Reported duration is less than one week, the arm is involved, the patient is a male aged 18–29, the patient considered this a rash, texture is reported as raised or bumpy, skin tone: Fitzpatrick III; lay graders estimated 3 on the Monk skin tone scale, this image was taken at an angle, the patient indicates itching — 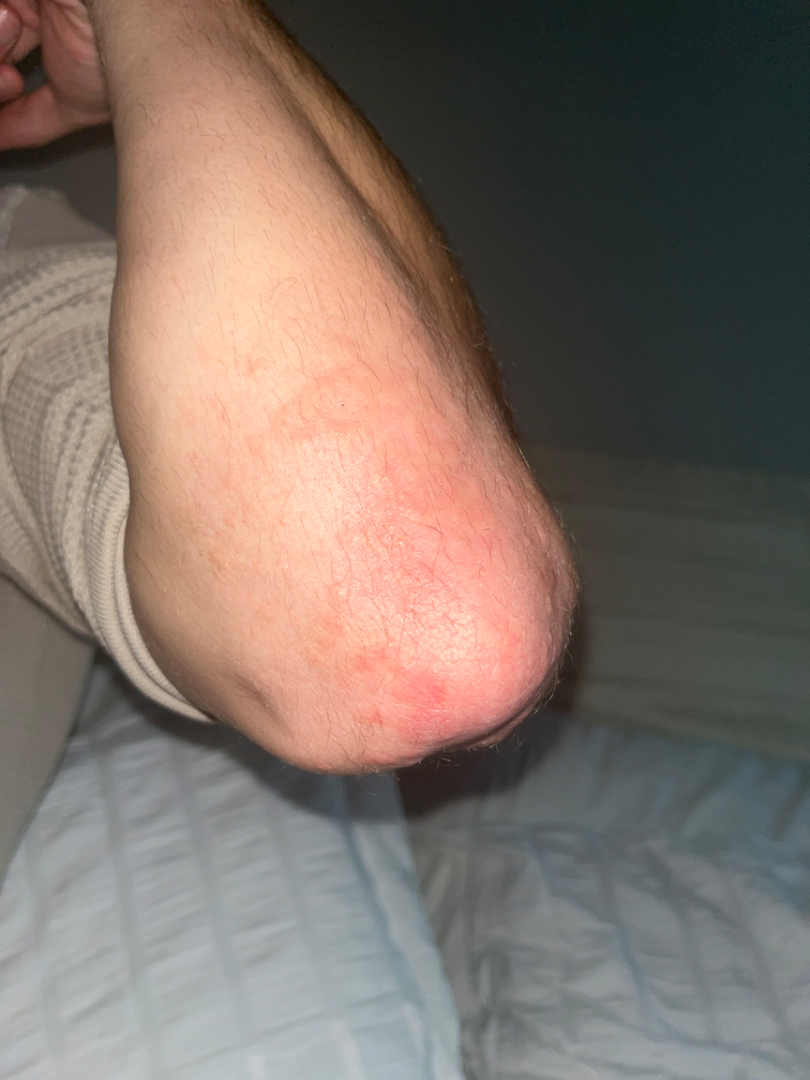Review:
The reviewer was unable to grade this case for skin condition.